The patient considered this a rash · the patient did not report lesion symptoms · texture is reported as rough or flaky · present for one to three months · the photograph was taken at a distance · the affected area is the back of the hand · Fitzpatrick IV; lay reviewers estimated MST 3 or 7 (two reviewer pools disagreed): 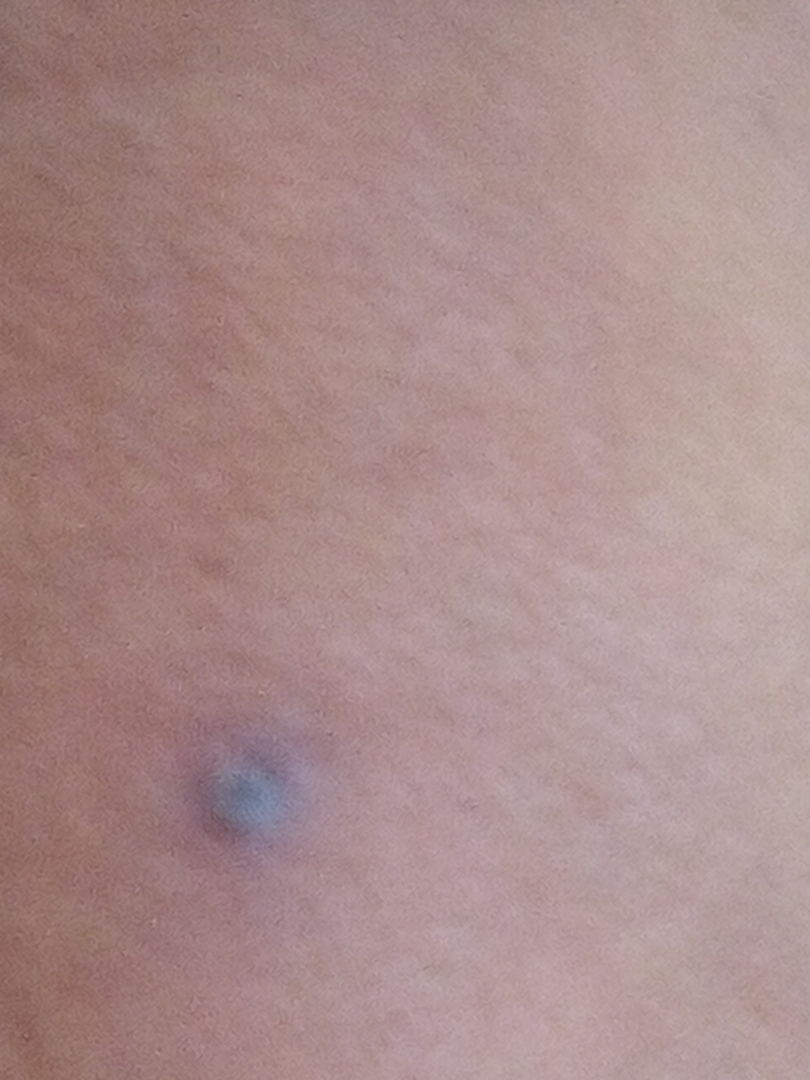| field | value |
|---|---|
| differential diagnosis | most likely Verruca vulgaris; also consider Lichen Simplex Chronicus |